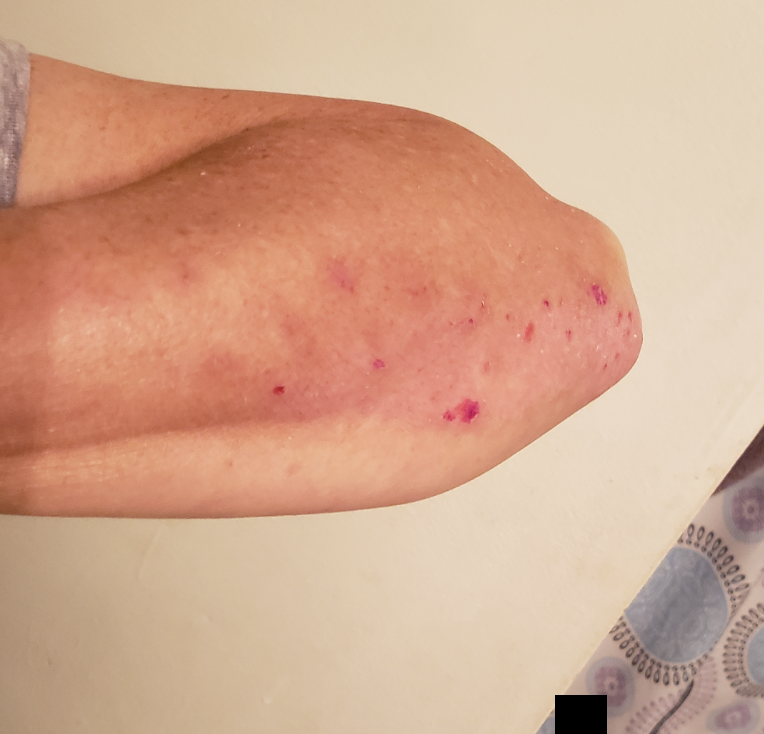Findings:
- body site · arm
- photo taken · at a distance
- surface texture · rough or flaky and raised or bumpy
- contributor · female, age 50–59
- dermatologist impression · in keeping with Psoriasis